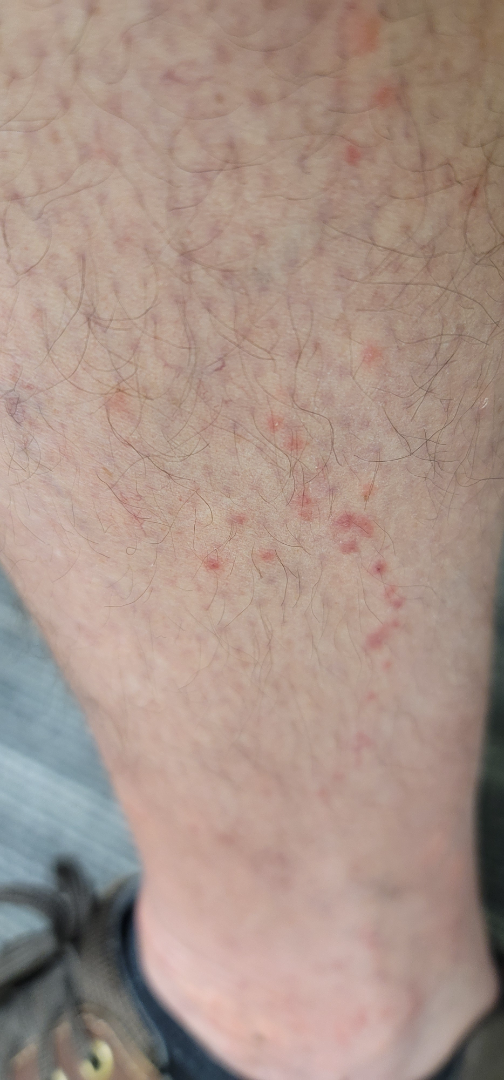Q: Could the case be diagnosed?
A: ungradable on photographic review
Q: What is the framing?
A: close-up